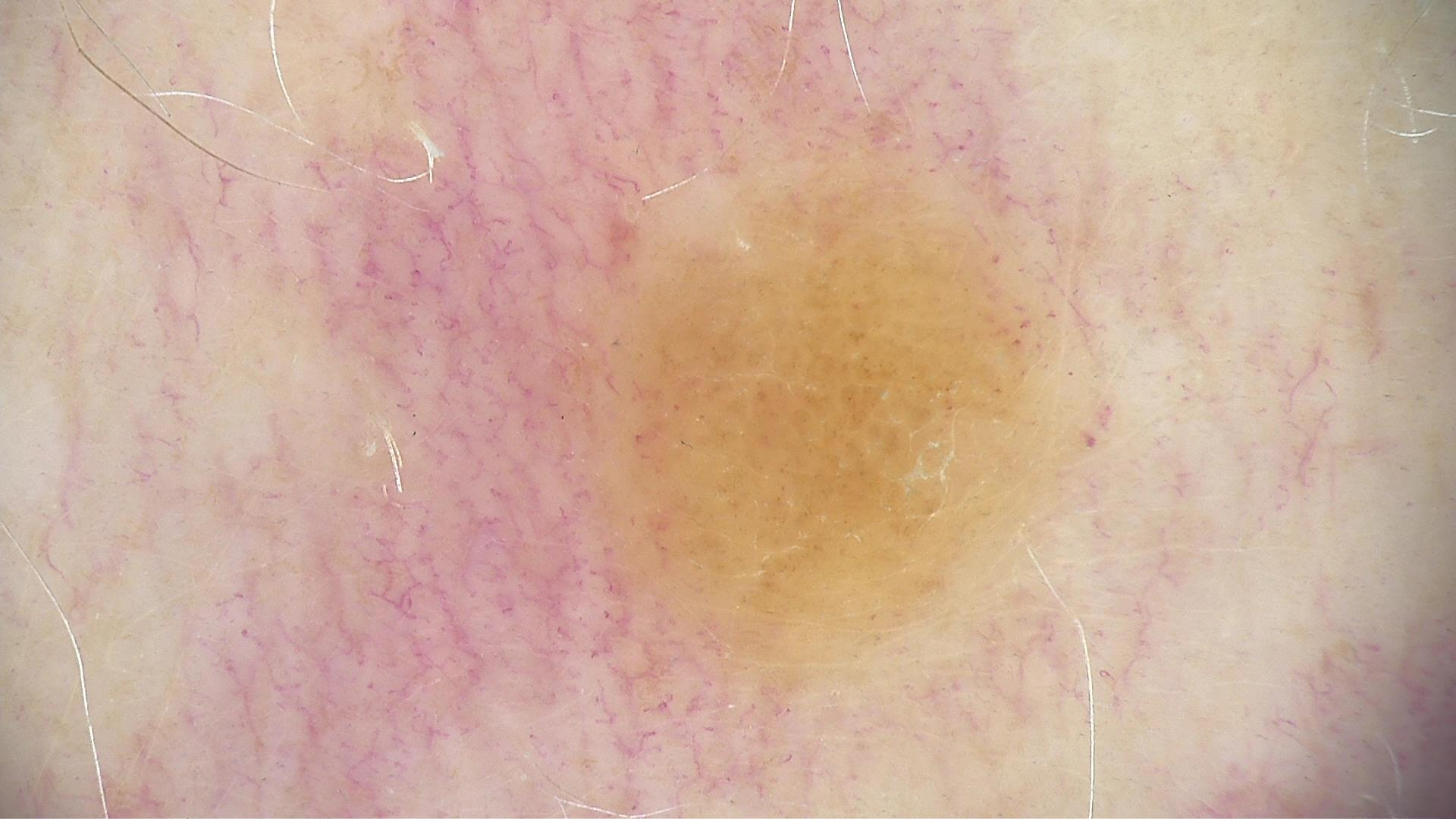assessment: dermal nevus (expert consensus)